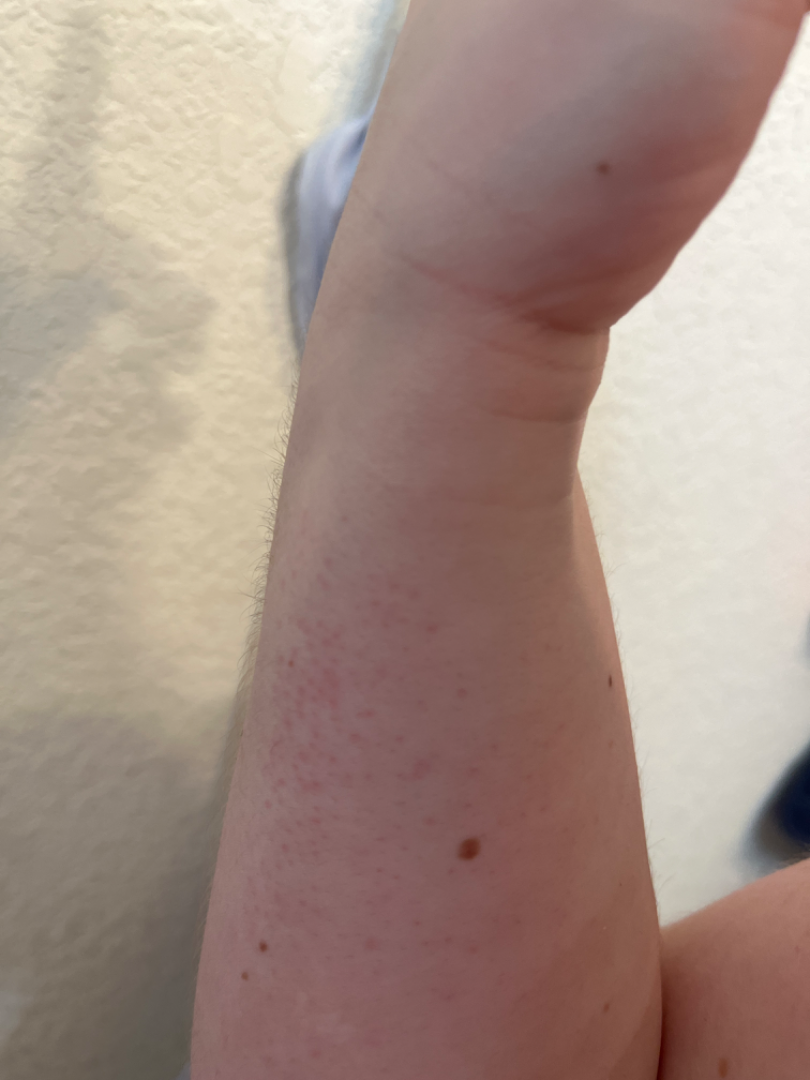impression = consistent with Keratosis pilaris